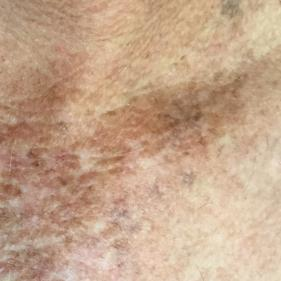• subject: aged 54
• region: the chest
• diagnosis: actinic keratosis (clinical consensus)